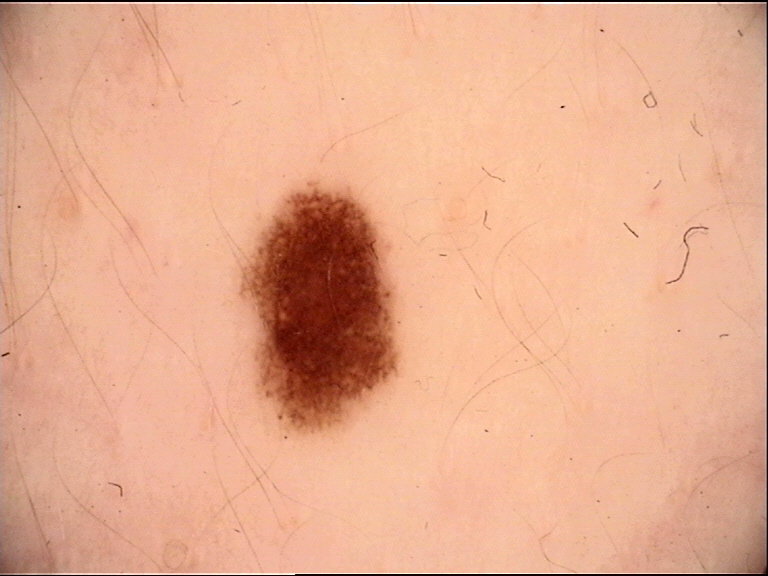<case>
  <diagnosis>
    <name>dysplastic junctional nevus</name>
    <code>jd</code>
    <malignancy>benign</malignancy>
    <super_class>melanocytic</super_class>
    <confirmation>expert consensus</confirmation>
  </diagnosis>
</case>